A clinical overview photograph of a skin lesion; a female subject aged 68-72 — 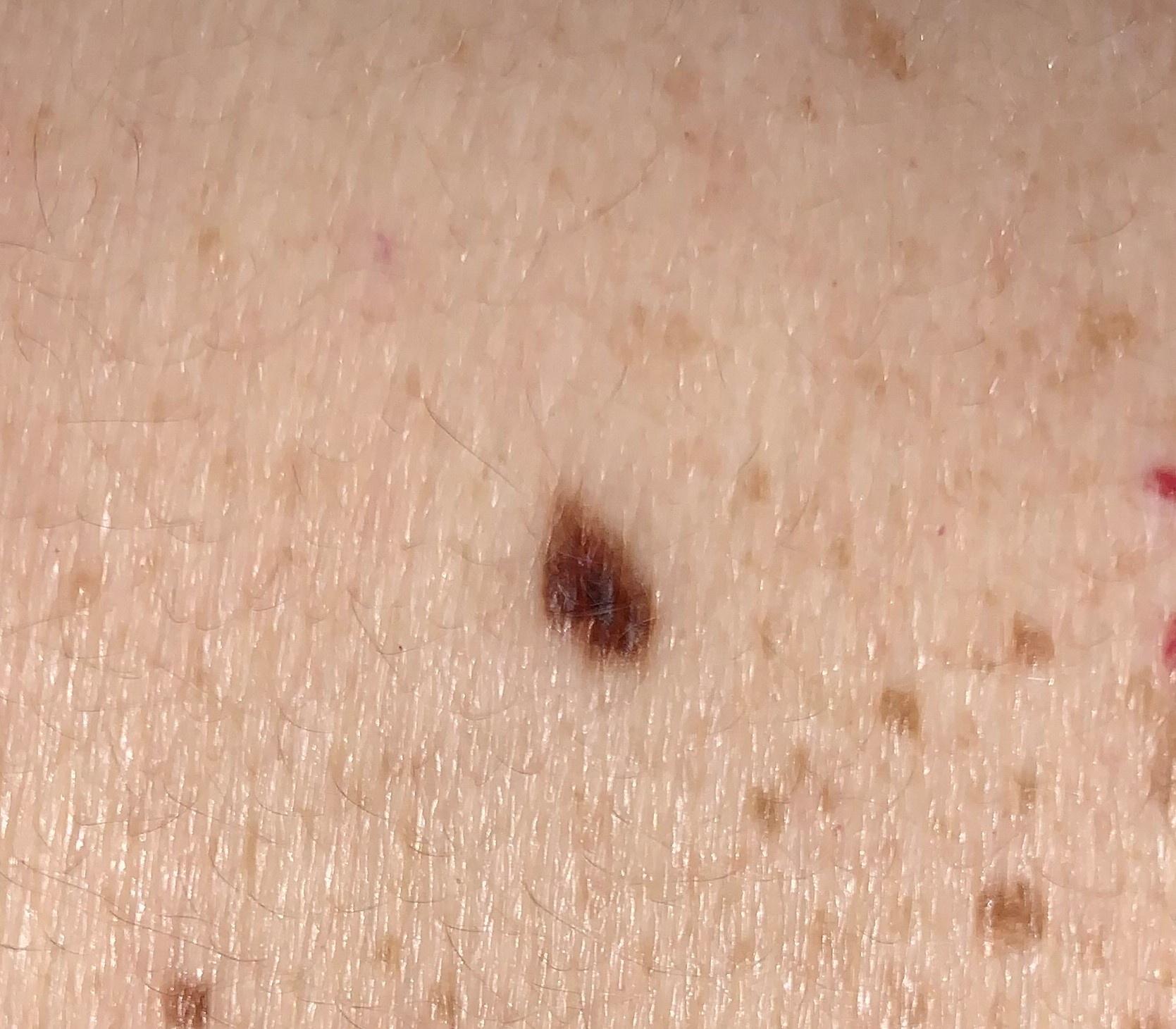The lesion was found on the trunk. Consistent with a nevus.